The subject is 70–79, female · close-up view.
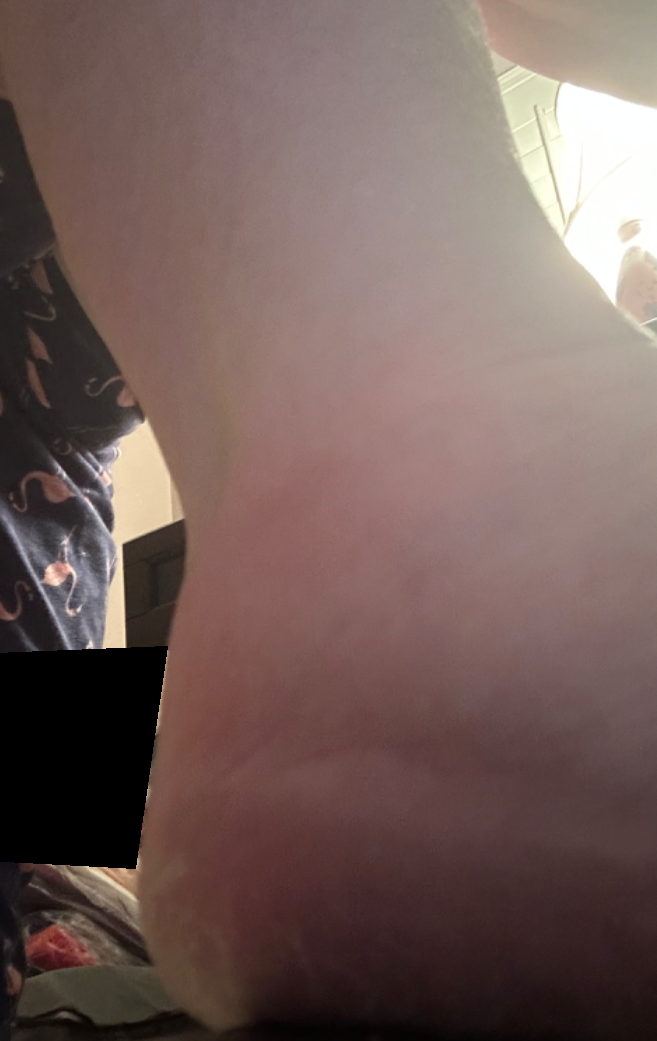The skin condition could not be confidently assessed from this image.